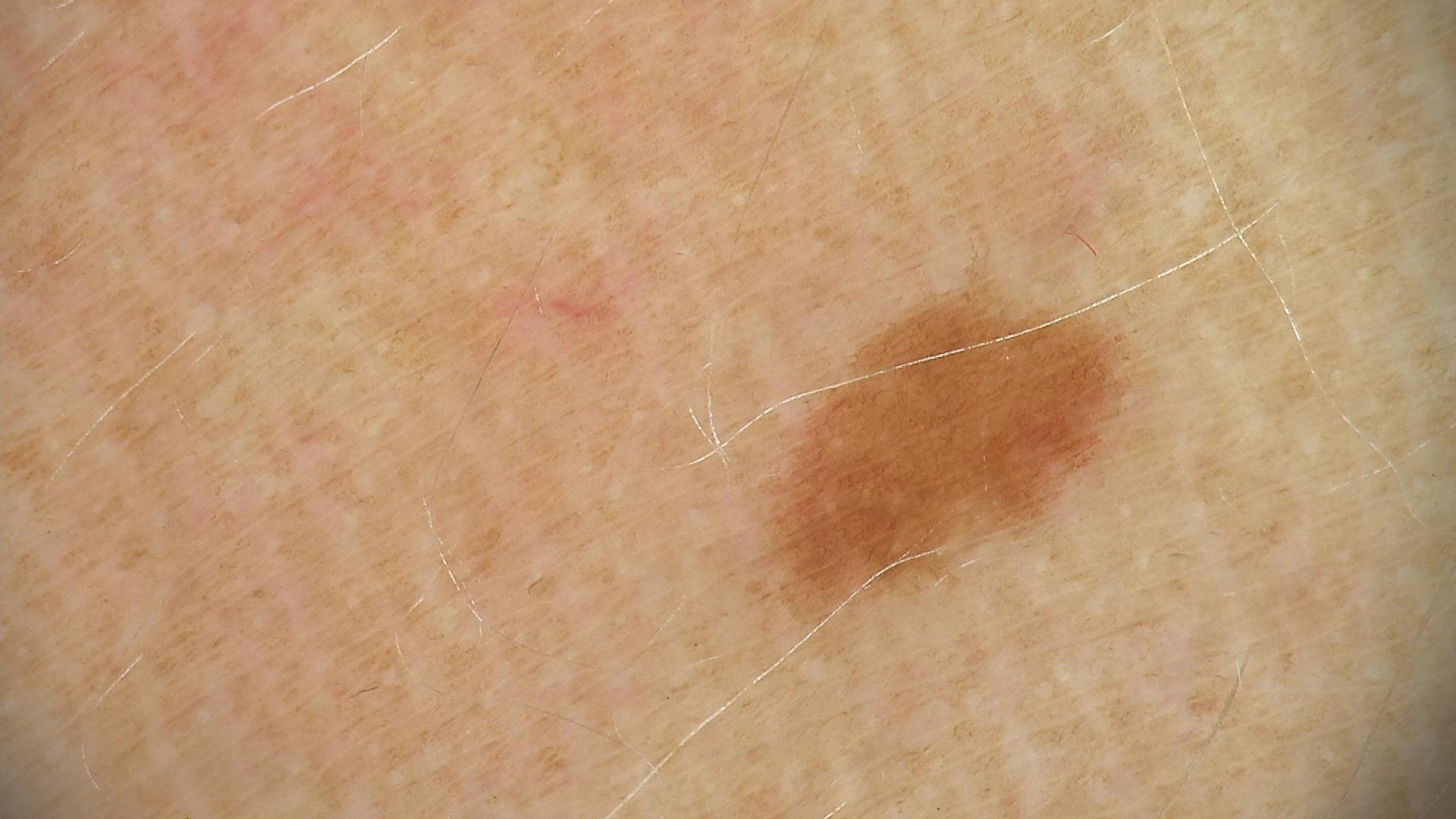- image: dermoscopy
- assessment: dysplastic junctional nevus (expert consensus)